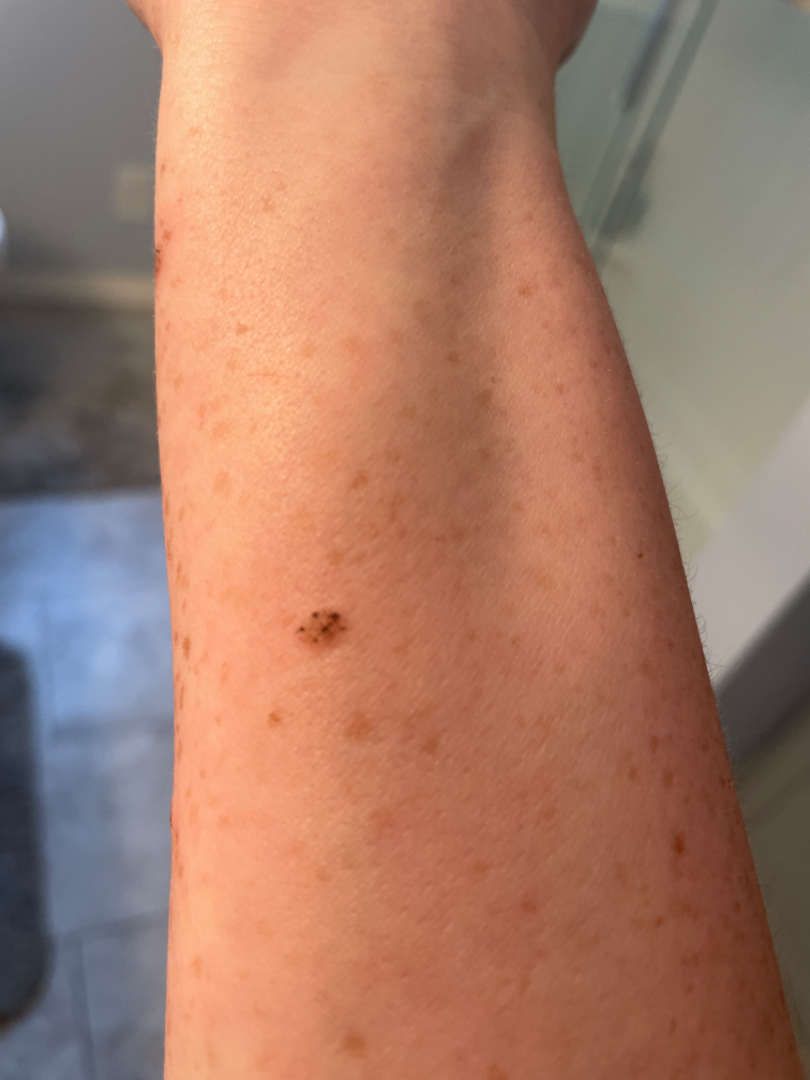History: The patient reports the lesion is raised or bumpy. No relevant lesion symptoms reported. The photograph is a close-up of the affected area. The patient is 30–39, female.